A dermoscopy image of a single skin lesion: 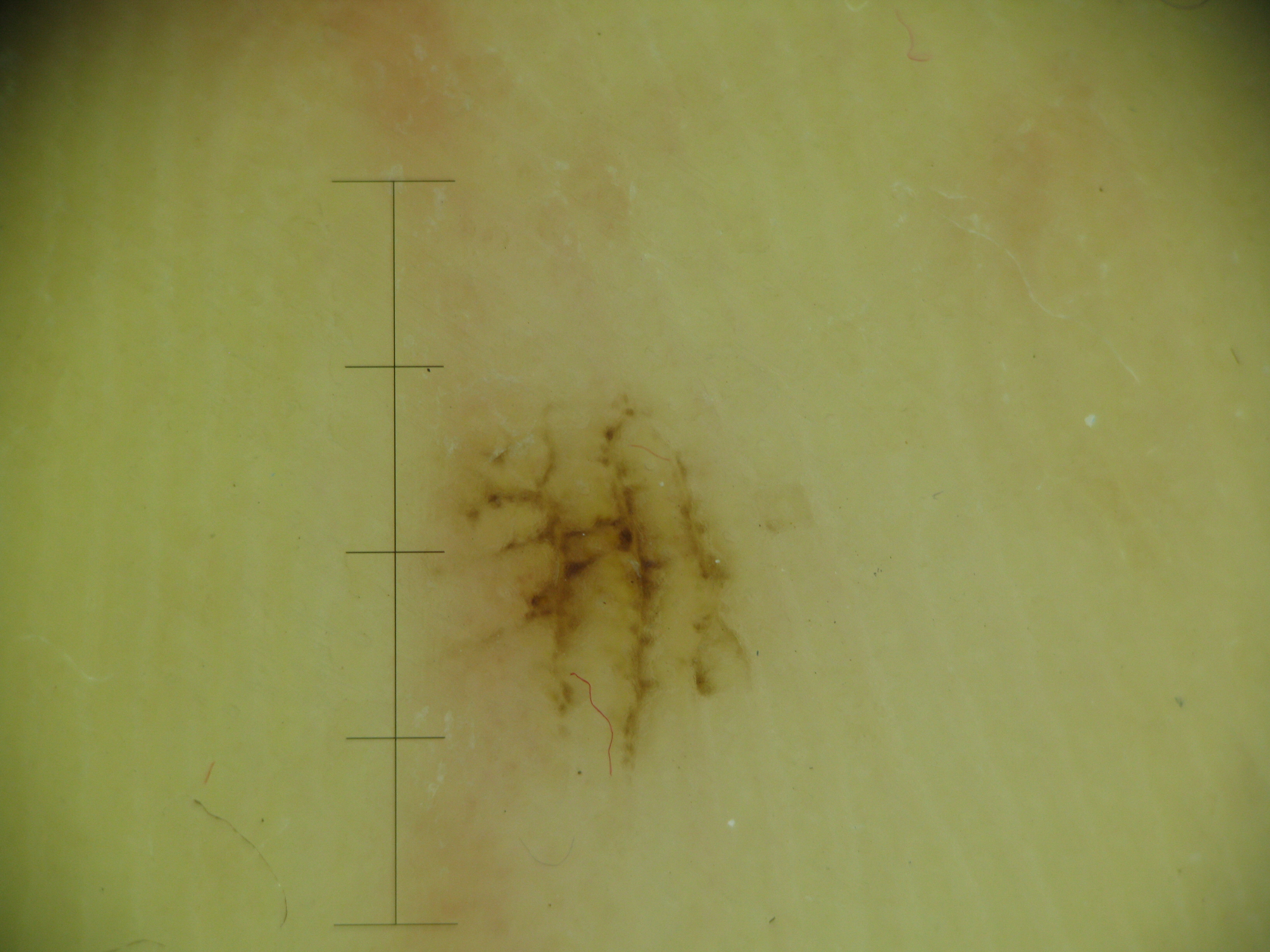{"diagnosis": {"name": "acral junctional nevus", "code": "ajb", "malignancy": "benign", "super_class": "melanocytic", "confirmation": "expert consensus"}}